The lesion involves the arm and back of the hand. The contributor is 18–29, male. This is a close-up image.
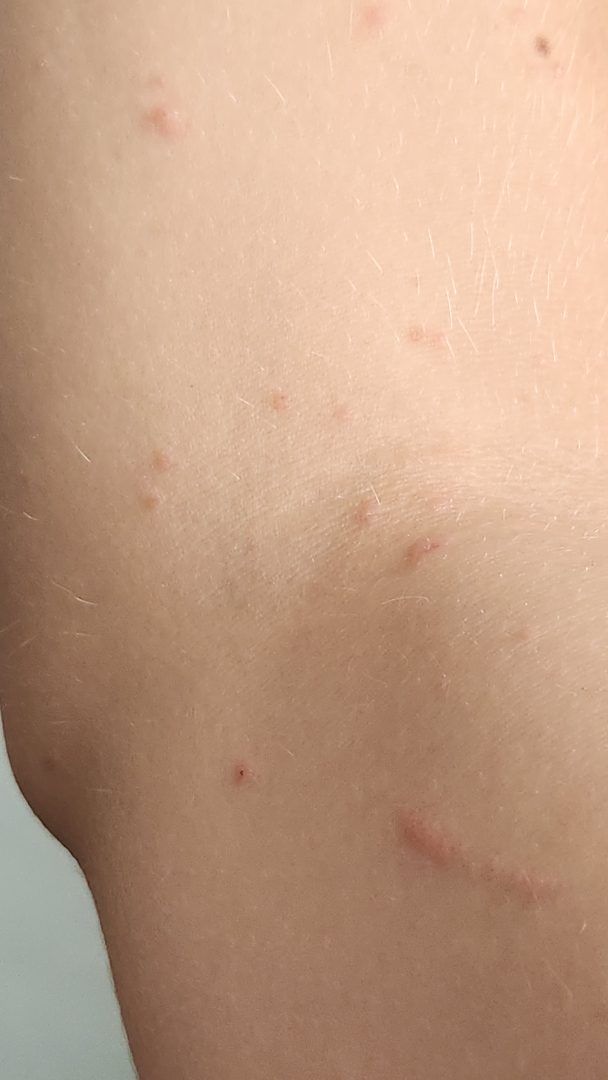Q: Reported symptoms?
A: itching
Q: Constitutional symptoms?
A: none reported
Q: When did this start?
A: one to four weeks
Q: How does the patient describe it?
A: a rash
Q: What is the differential diagnosis?
A: one reviewing dermatologist: the leading impression is Scabies; also raised was Insect Bite; also consider Hypersensitivity